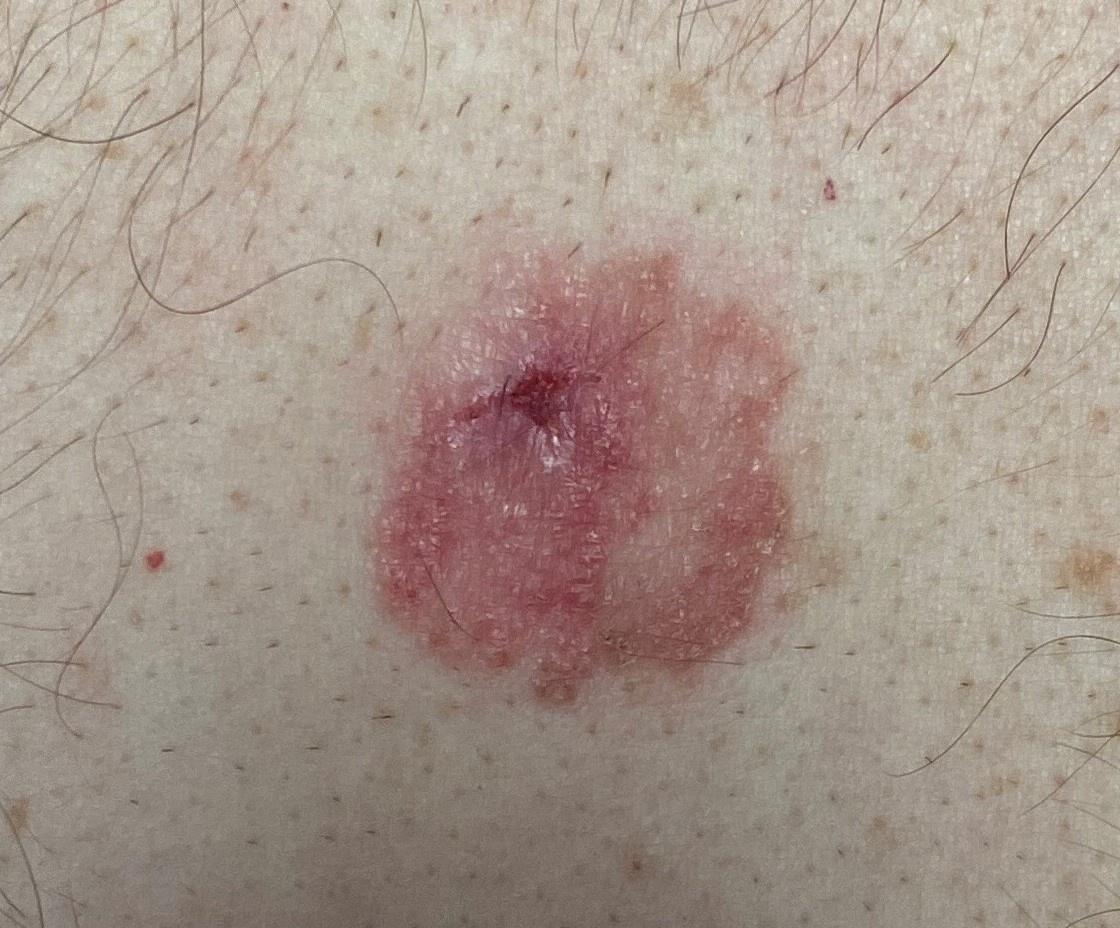<case>
  <patient>
    <age_approx>65</age_approx>
    <sex>male</sex>
  </patient>
  <image>clinical photograph</image>
  <skin_type>II</skin_type>
  <lesion_location>
    <region>the trunk</region>
    <detail>the anterior trunk</detail>
  </lesion_location>
  <diagnosis>
    <name>Basal cell carcinoma</name>
    <malignancy>malignant</malignancy>
    <confirmation>histopathology</confirmation>
    <lineage>adnexal</lineage>
  </diagnosis>
</case>